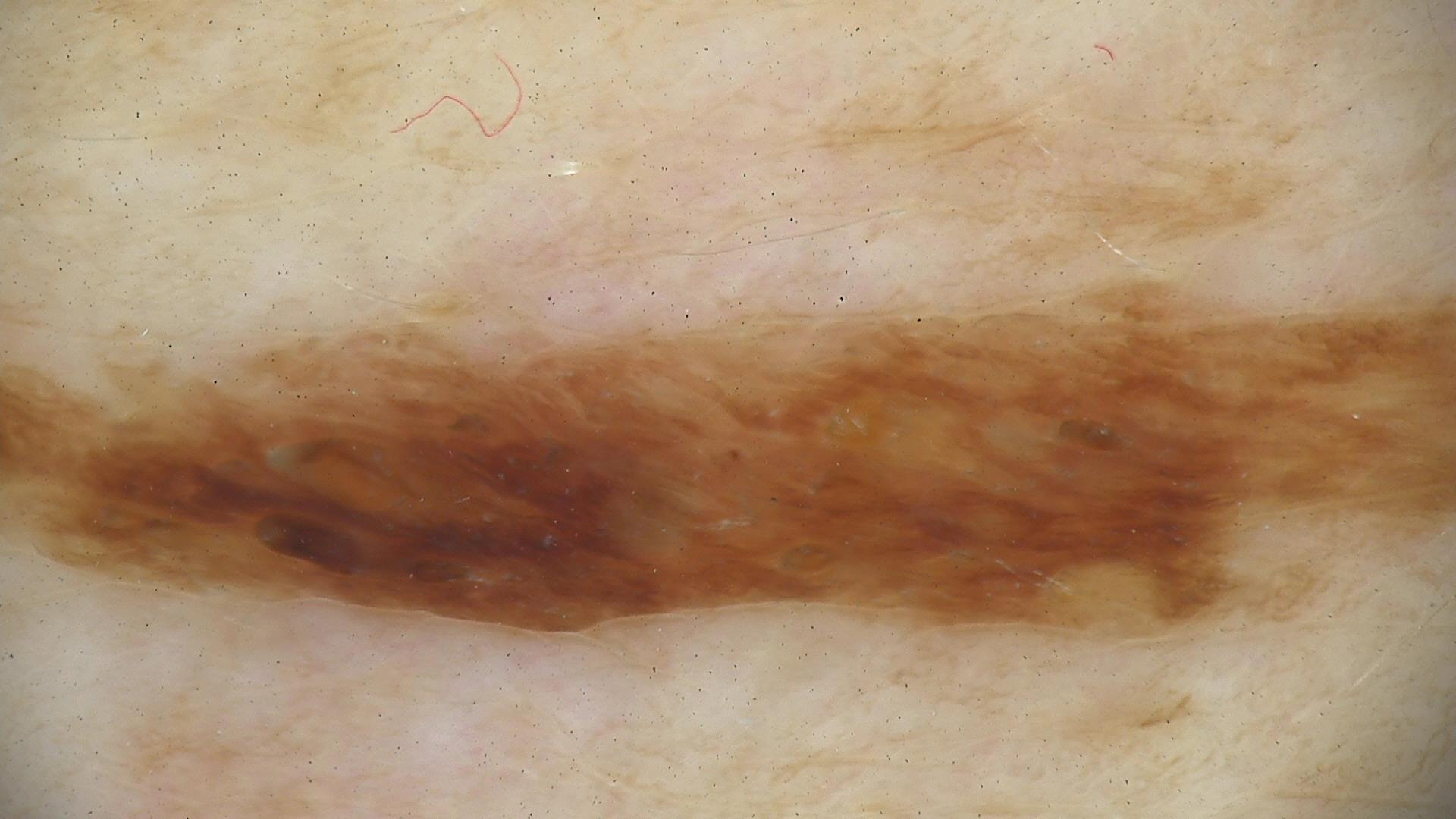Findings:
A skin lesion imaged with a dermatoscope. This is a keratinocytic lesion.
Impression:
Consistent with a benign lesion — a seborrheic keratosis.